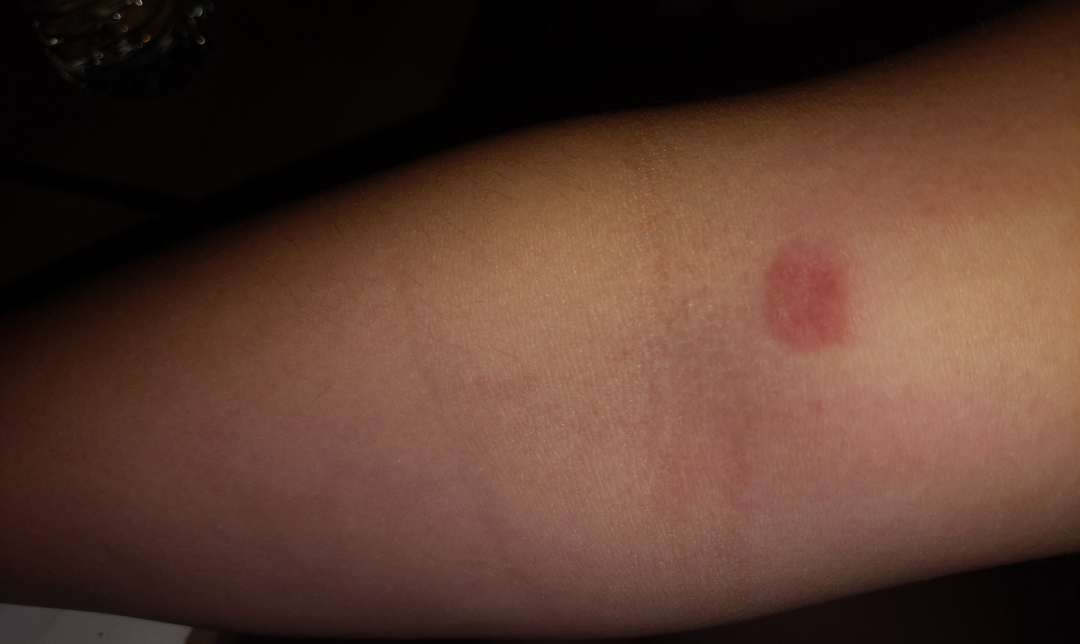Notes:
• anatomic site — arm
• photo taken — at a distance
• surface texture — raised or bumpy and fluid-filled
• subject — female, age 18–29
• patient's own categorization — a rash
• constitutional symptoms — none reported
• assessment — reviewed remotely by three dermatologists: the leading impression is Eczema; possibly Insect Bite; lower on the differential is Allergic Contact Dermatitis; less likely is Pityriasis rosea